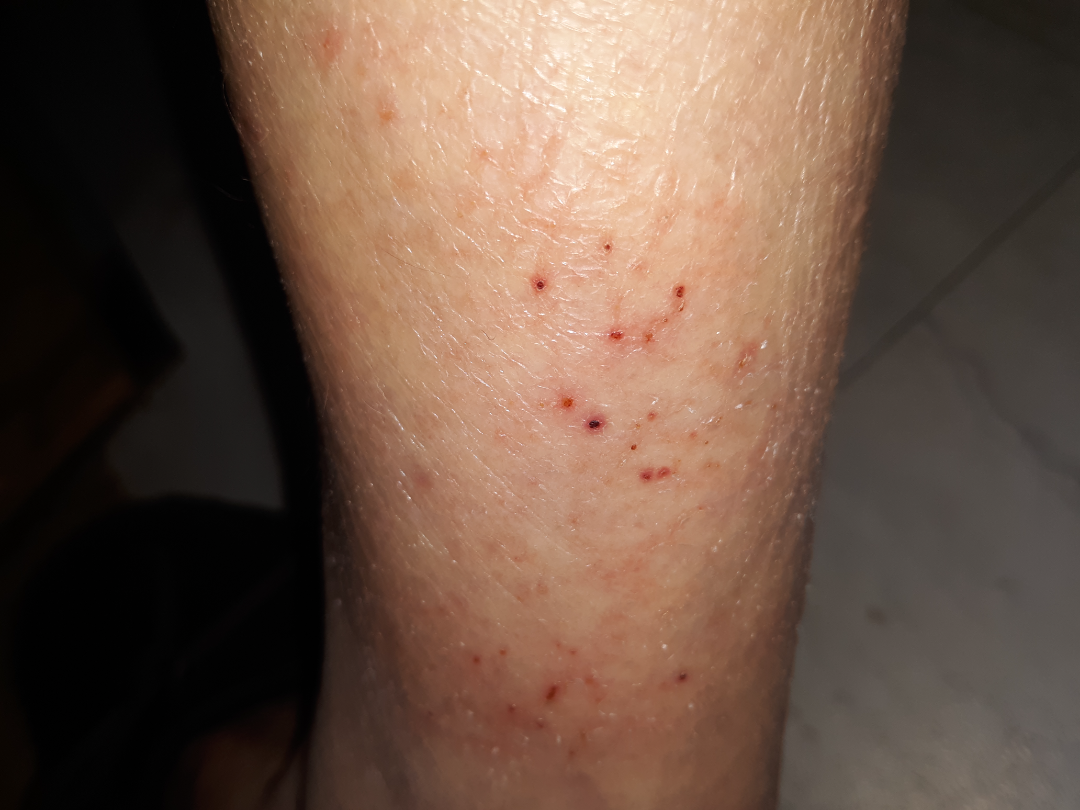Notes:
– dermatologist impression: the differential is split between Xerosis and Eczema